Present for one to four weeks · the lesion involves the back of the torso · reported lesion symptoms include itching · the photograph was taken at an angle — 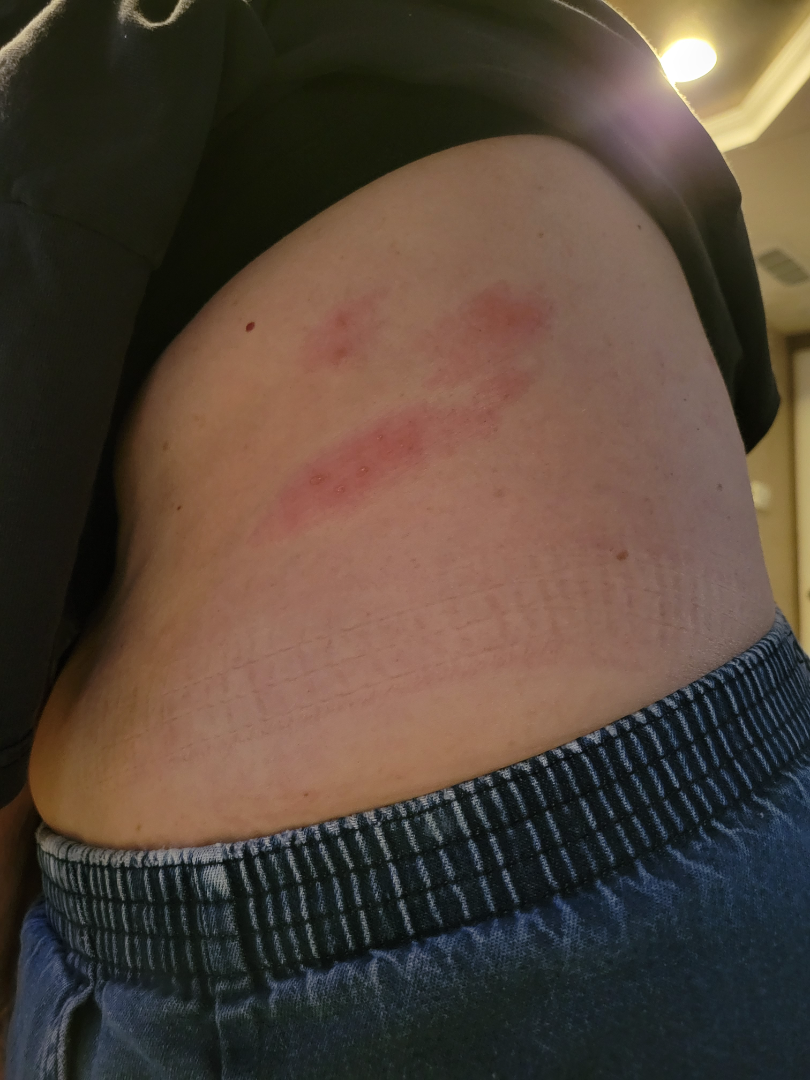| feature | finding |
|---|---|
| clinical impression | most consistent with Herpes Zoster |